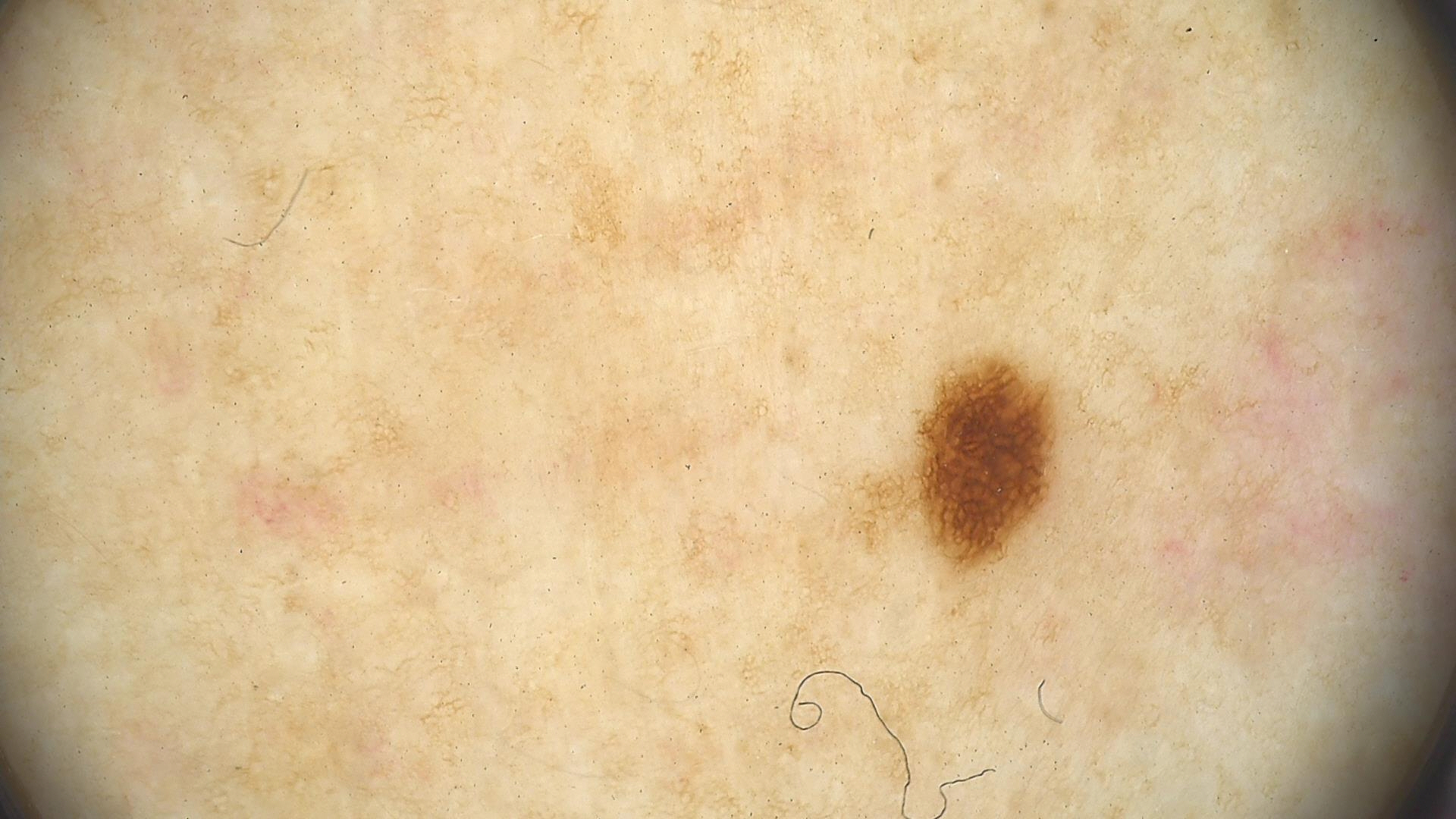Dermoscopy of a skin lesion. Classified as a banal lesion — a junctional nevus.